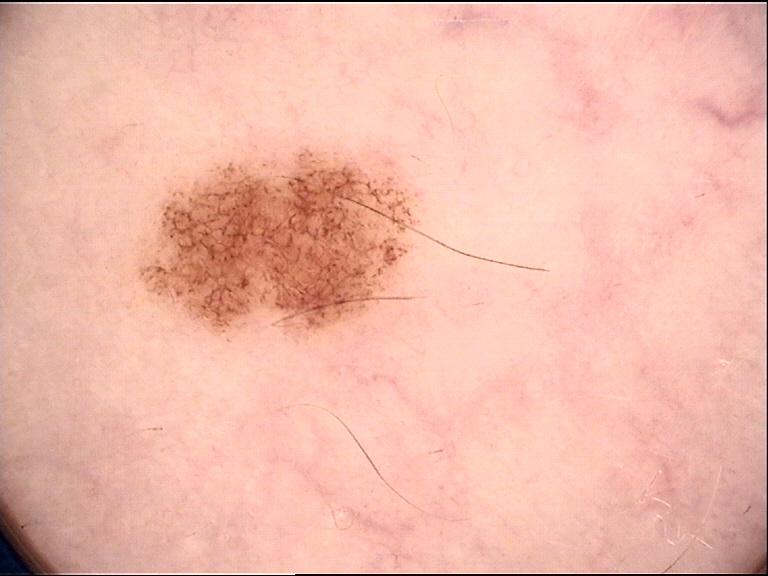image: dermoscopy
diagnosis:
  name: dysplastic junctional nevus
  code: jd
  malignancy: benign
  super_class: melanocytic
  confirmation: expert consensus